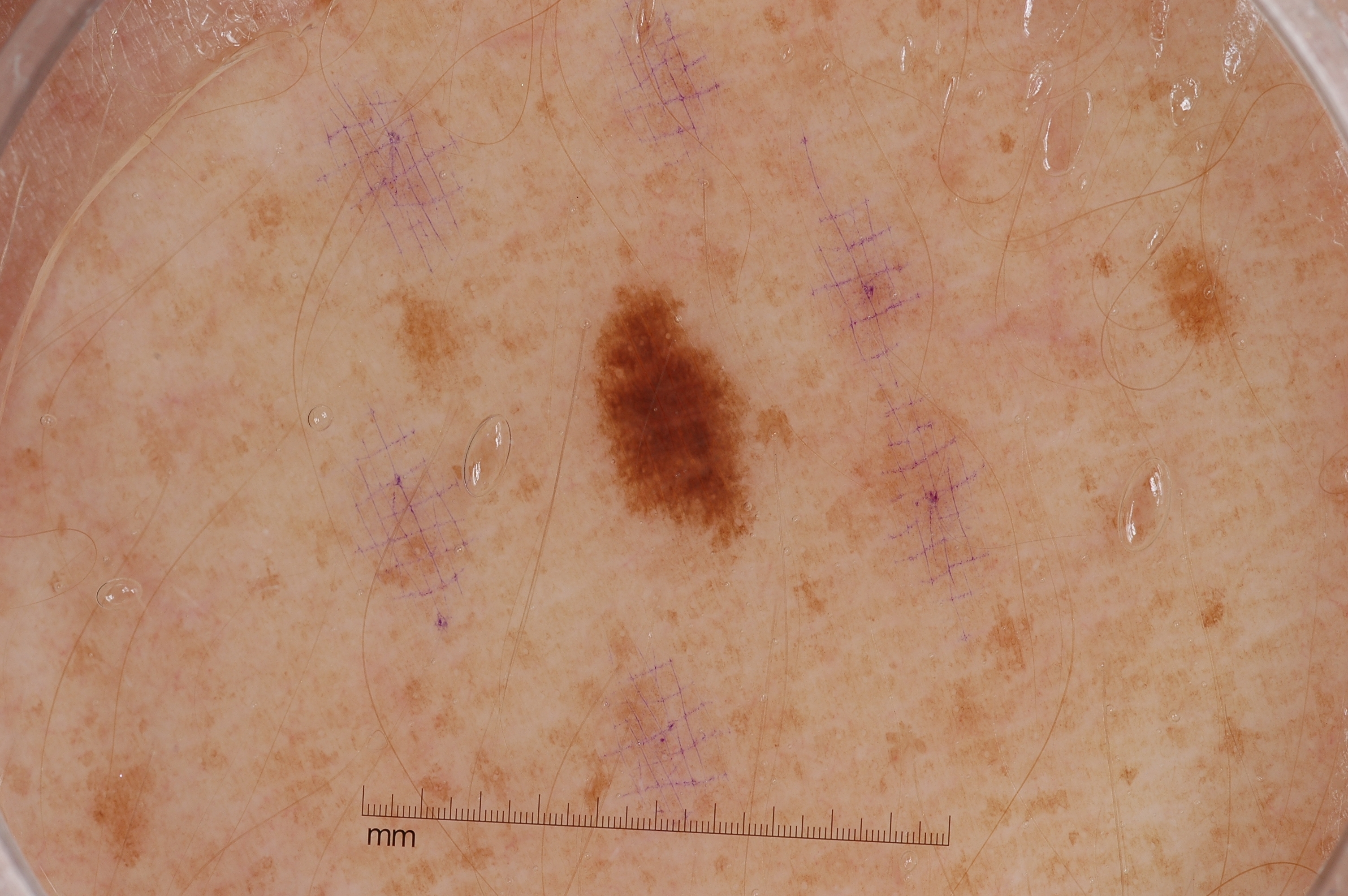A dermoscopy image of a single skin lesion. A female subject, approximately 25 years of age. The lesion covers approximately 2% of the dermoscopic field. The lesion's extent is 588/283/751/549. Dermoscopic assessment notes pigment network, with no streaks, milia-like cysts, or negative network. Clinically diagnosed as a melanocytic nevus.